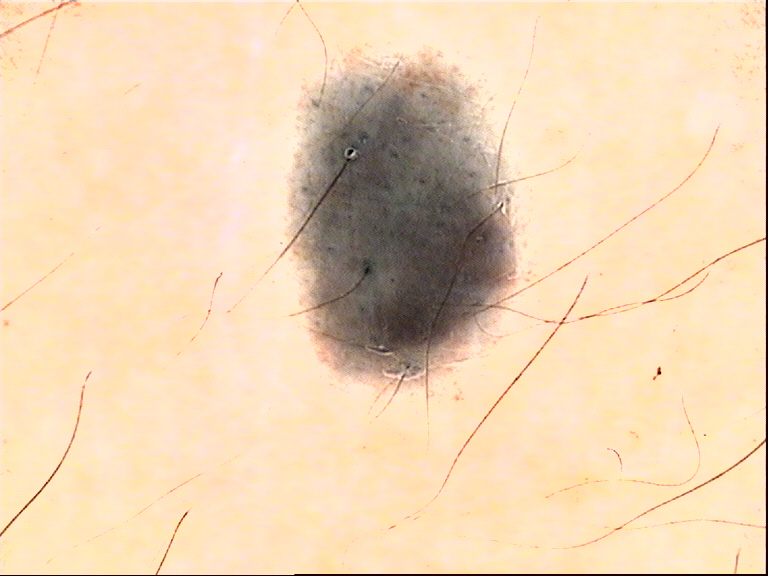A dermoscopic image of a skin lesion.
The diagnosis was a banal lesion — a blue nevus.